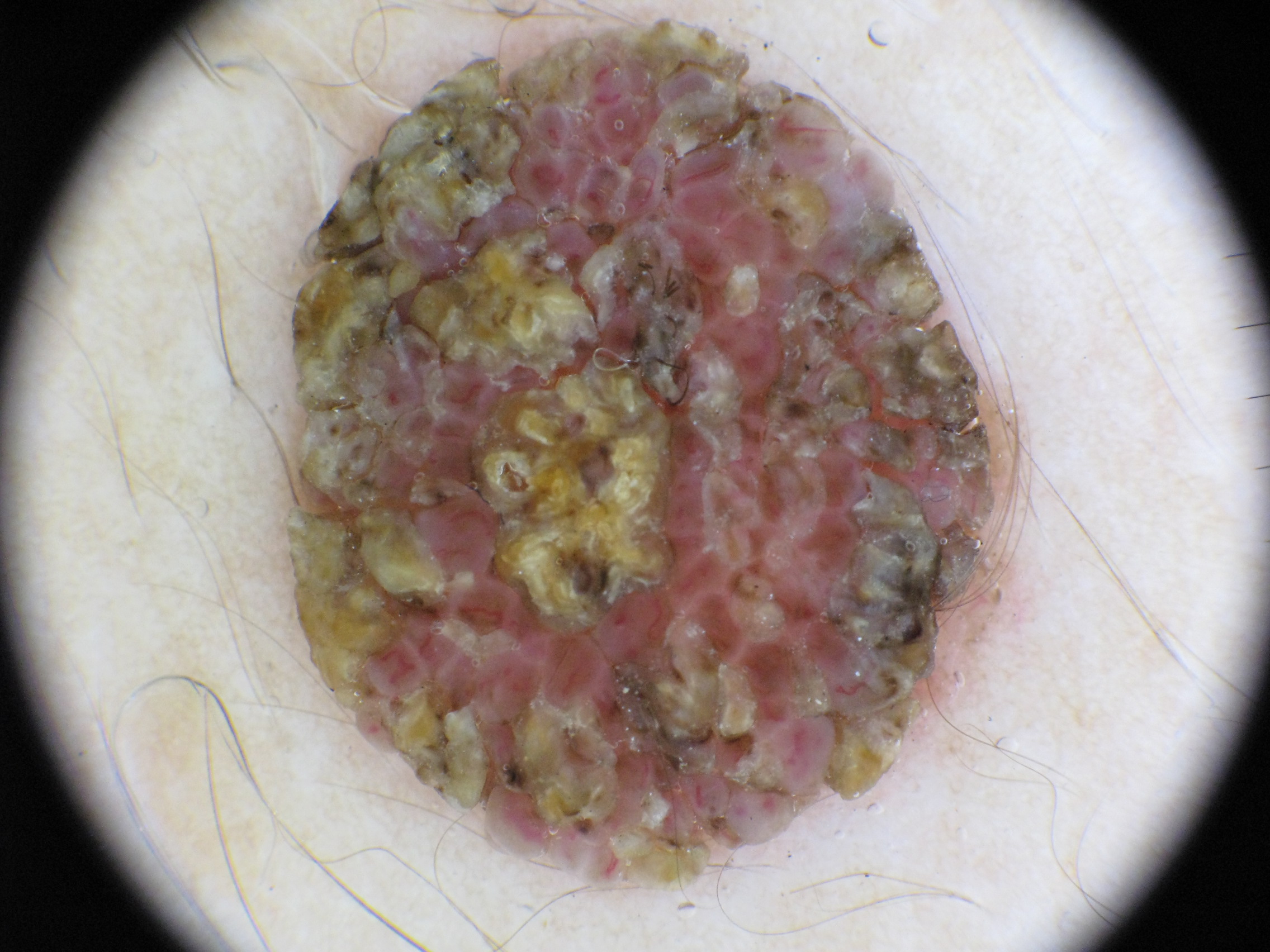Summary: A dermoscopy image of a single skin lesion. The dermoscopic pattern shows no milia-like cysts, negative network, streaks, pigment network, or globules. The lesion spans x1=279 y1=21 x2=1020 y2=880. Conclusion: Consistent with a melanocytic nevus, a benign lesion.